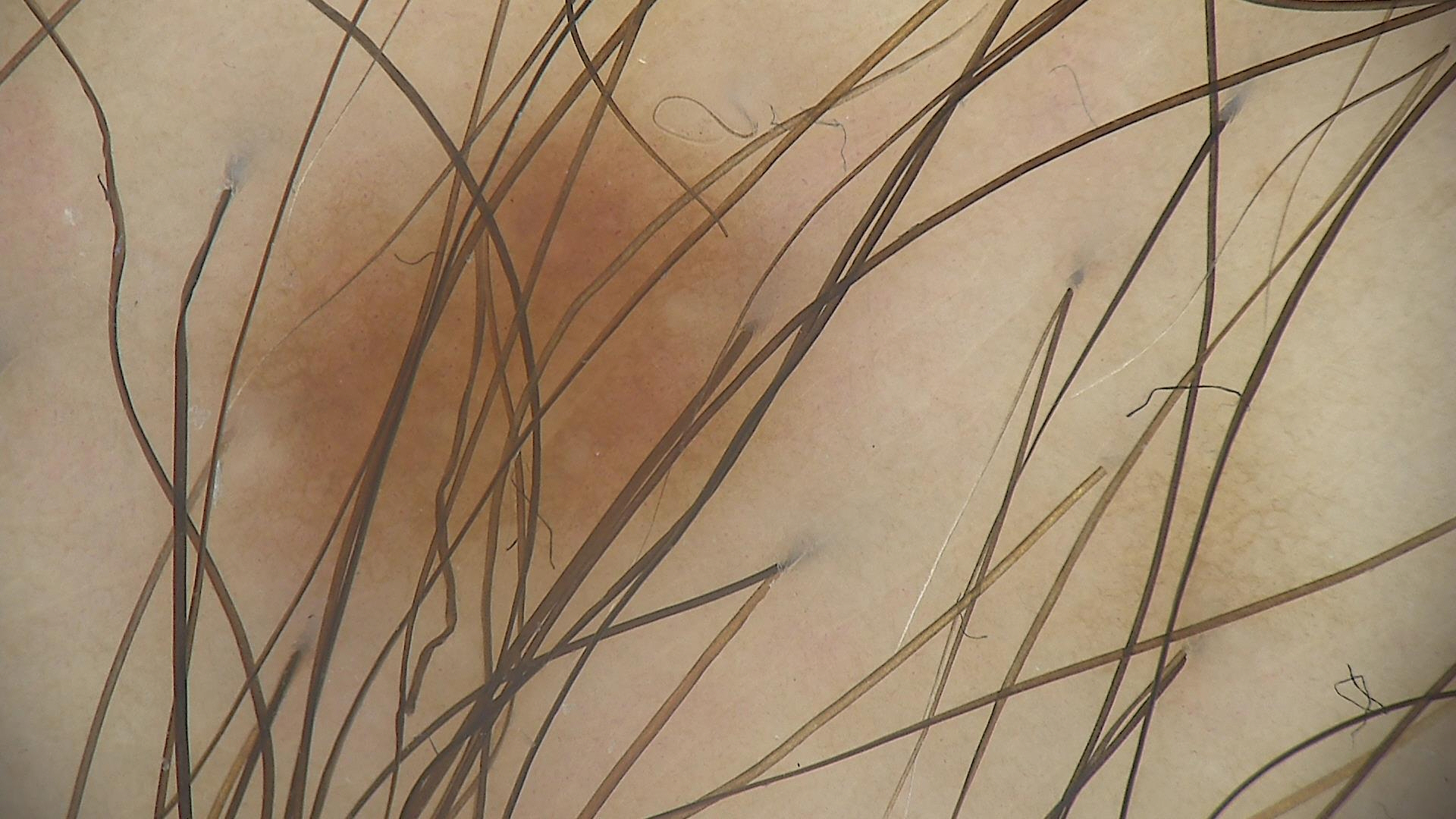The diagnosis was a banal lesion — a junctional nevus.